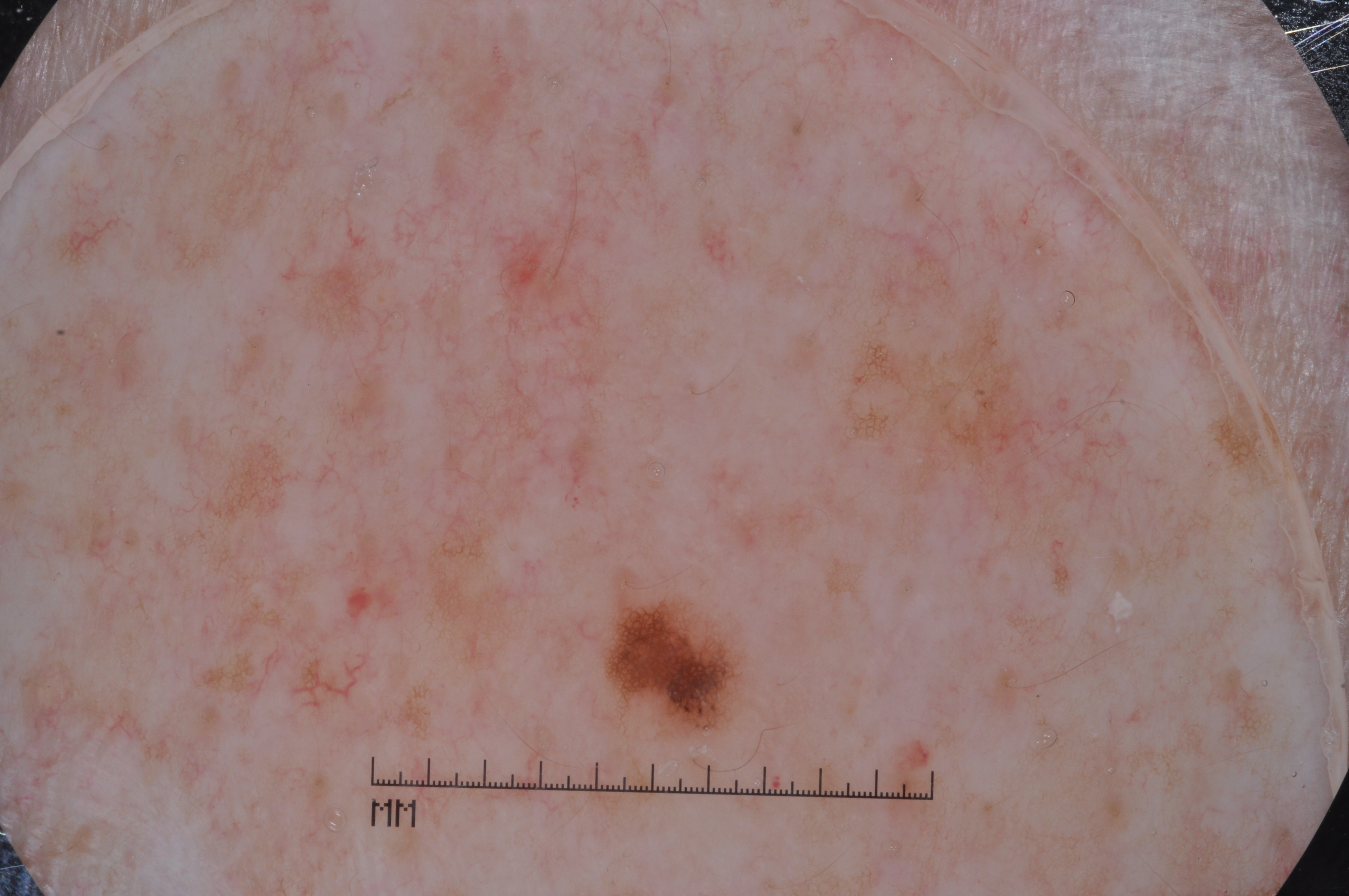Q: What kind of image is this?
A: dermoscopic image
Q: Where is the lesion in the image?
A: 601 581 742 736
Q: What did the assessment conclude?
A: a melanocytic nevus, a benign lesion